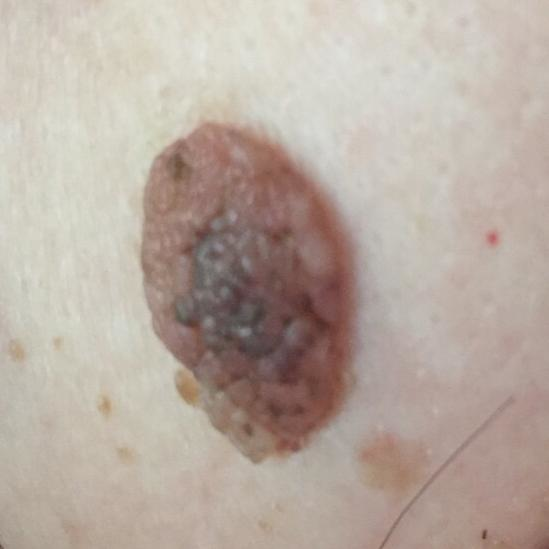image: smartphone clinical photo; symptoms: growth, elevation; diagnostic label: nevus (clinical consensus).